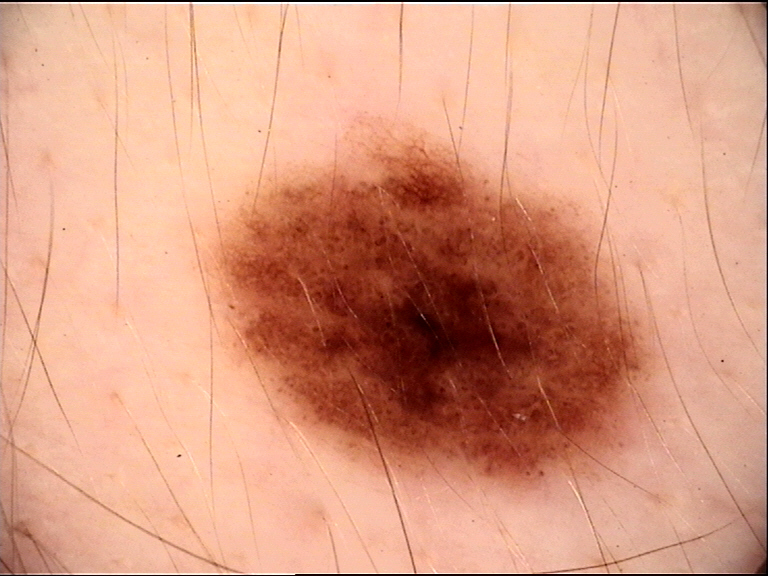label = dysplastic junctional nevus (expert consensus).